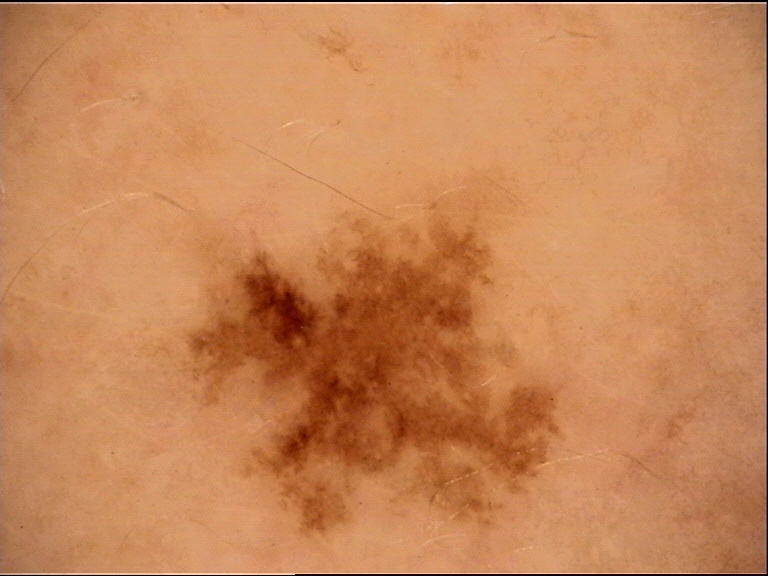Impression:
Classified as a dysplastic junctional nevus.